A dermatoscopic image of a skin lesion.
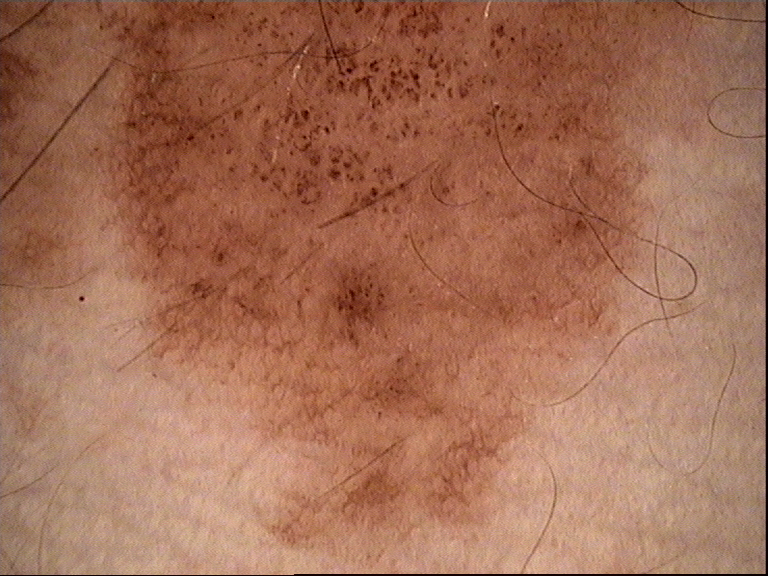Labeled as a banal lesion — a congenital junctional nevus.